Symptoms reported: itching. This is a close-up image. Texture is reported as raised or bumpy. Reported duration is less than one week. The patient is 30–39, female. The lesion involves the back of the torso, back of the hand and arm:
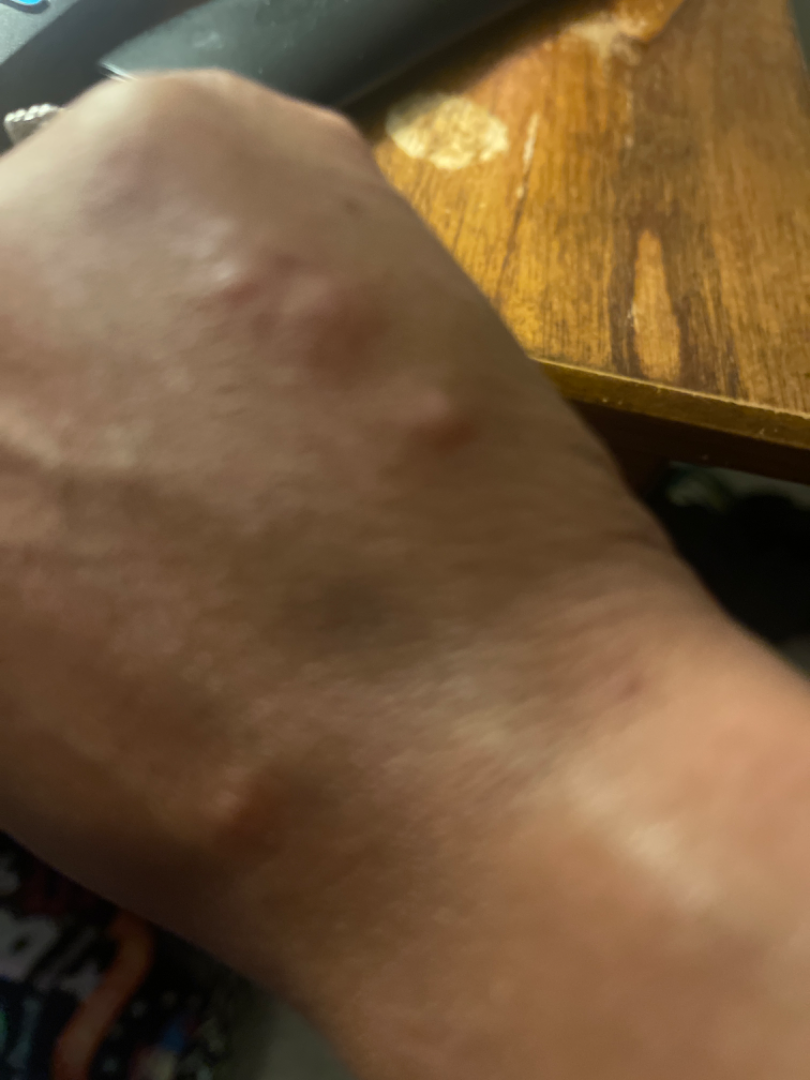Findings:
On dermatologist assessment of the image: Insect Bite (primary).